Male contributor, age 18–29 · the photo was captured at an angle · located on the leg:
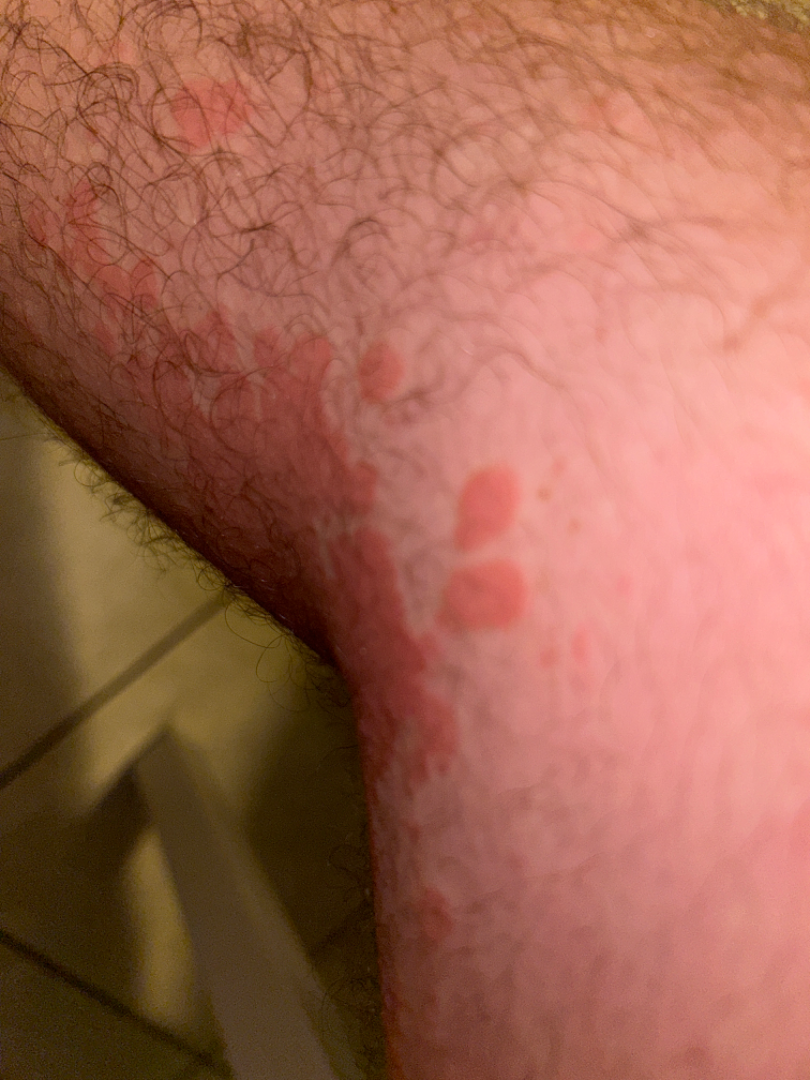On dermatologist assessment of the image: Tinea Versicolor (44%); Psoriasis (44%); Eczema (12%).